A dermoscopy image of a skin lesion. The patient says their skin tans without first burning. A female subject 84 years old. By self-report, a personal history of cancer and no immunosuppression. Acquired for a research image collection, with no referral diagnosis — 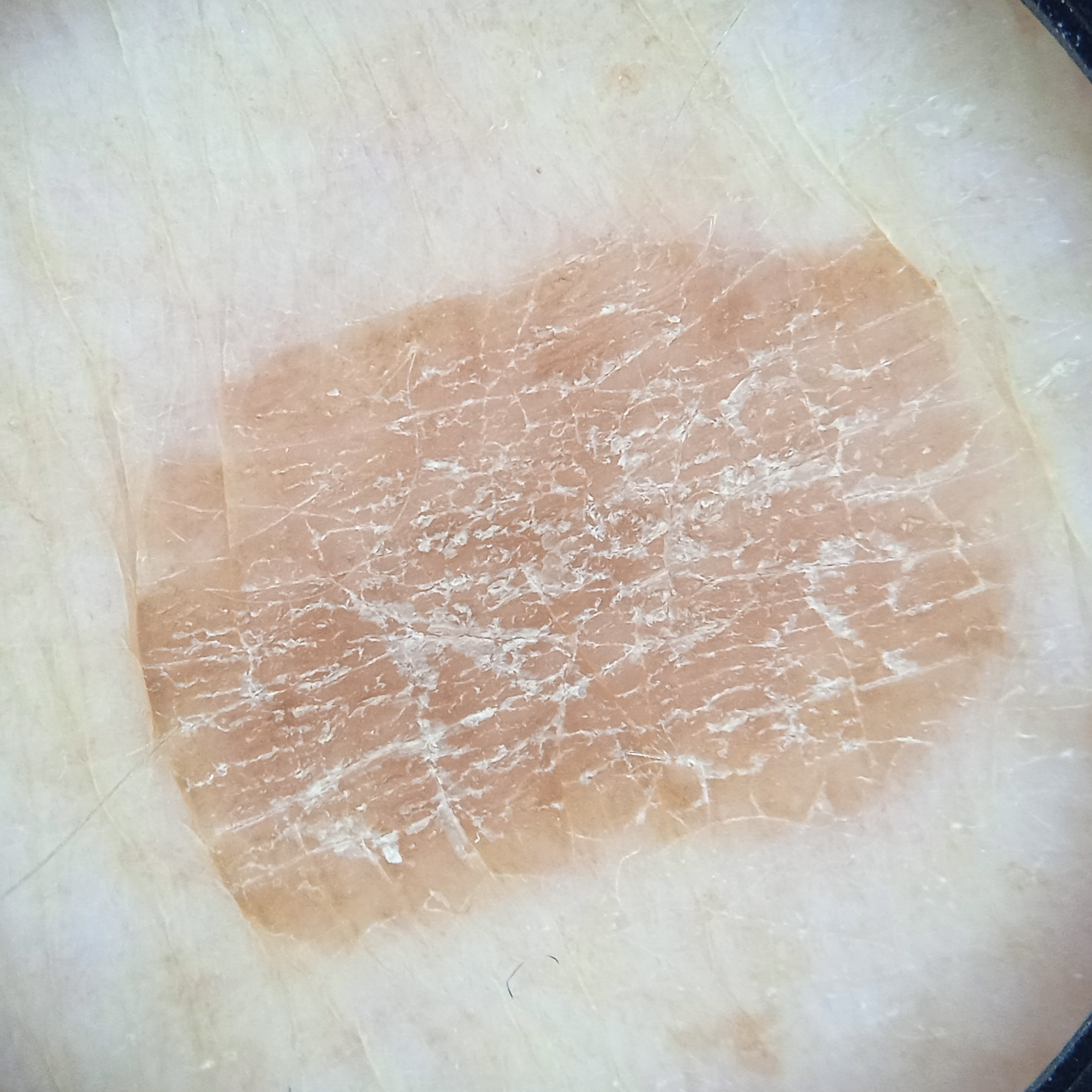Q: What is the anatomic site?
A: an arm
Q: Lesion size?
A: 11.2 mm
Q: What was the diagnosis?
A: seborrheic keratosis (dermatologist consensus)